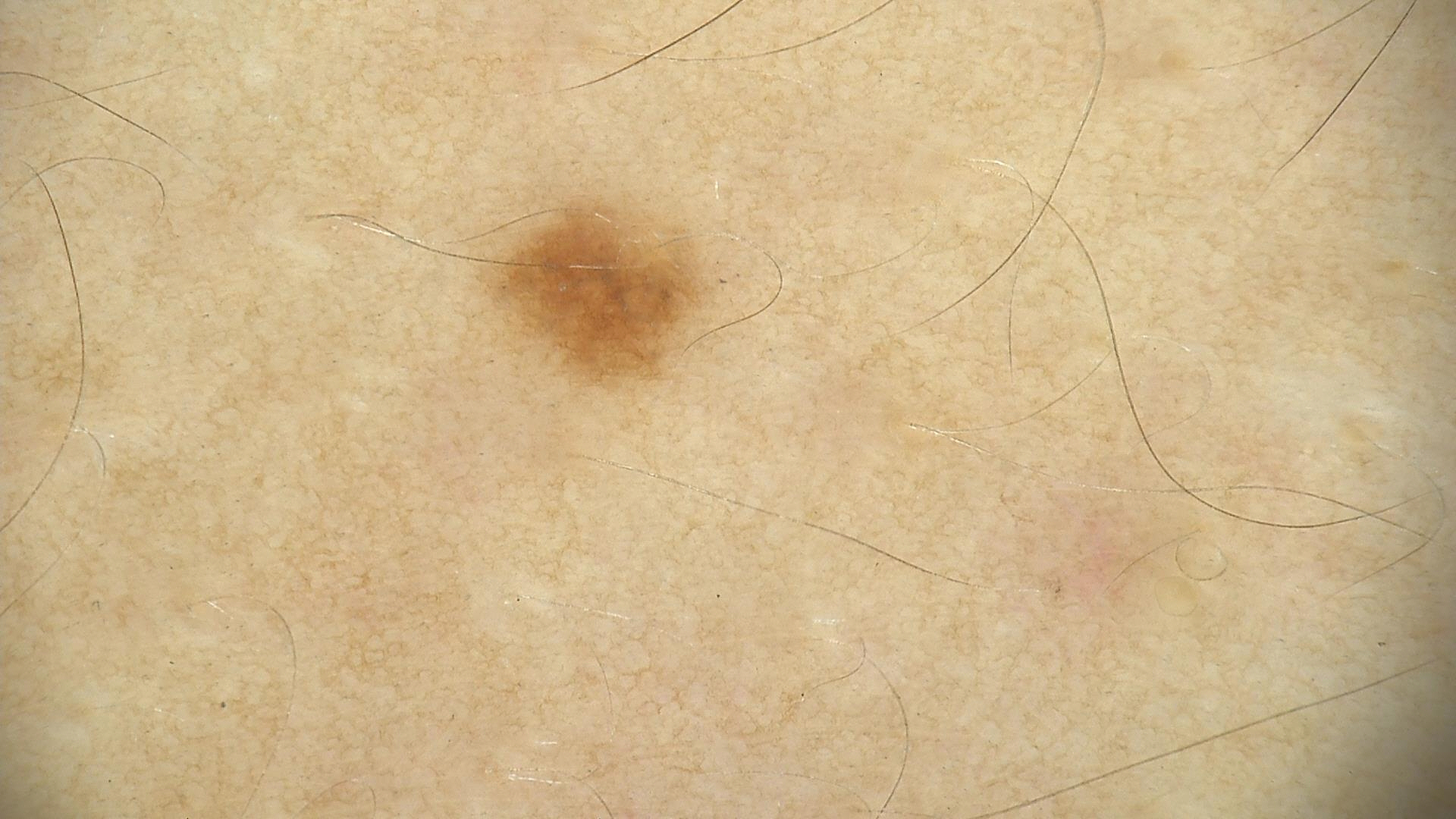A dermoscopy image of a single skin lesion. The diagnosis was a dysplastic junctional nevus.